Recorded as skin type II. A female patient in their mid- to late 60s. A wide-field clinical photograph of a skin lesion.
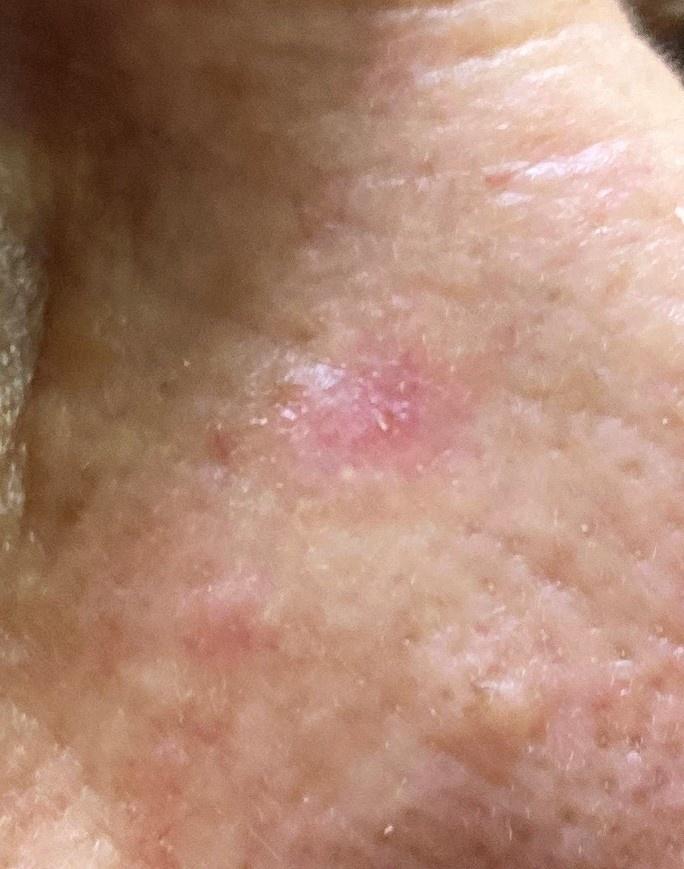• anatomic site: the head or neck
• pathology: Basal cell carcinoma (biopsy-proven)